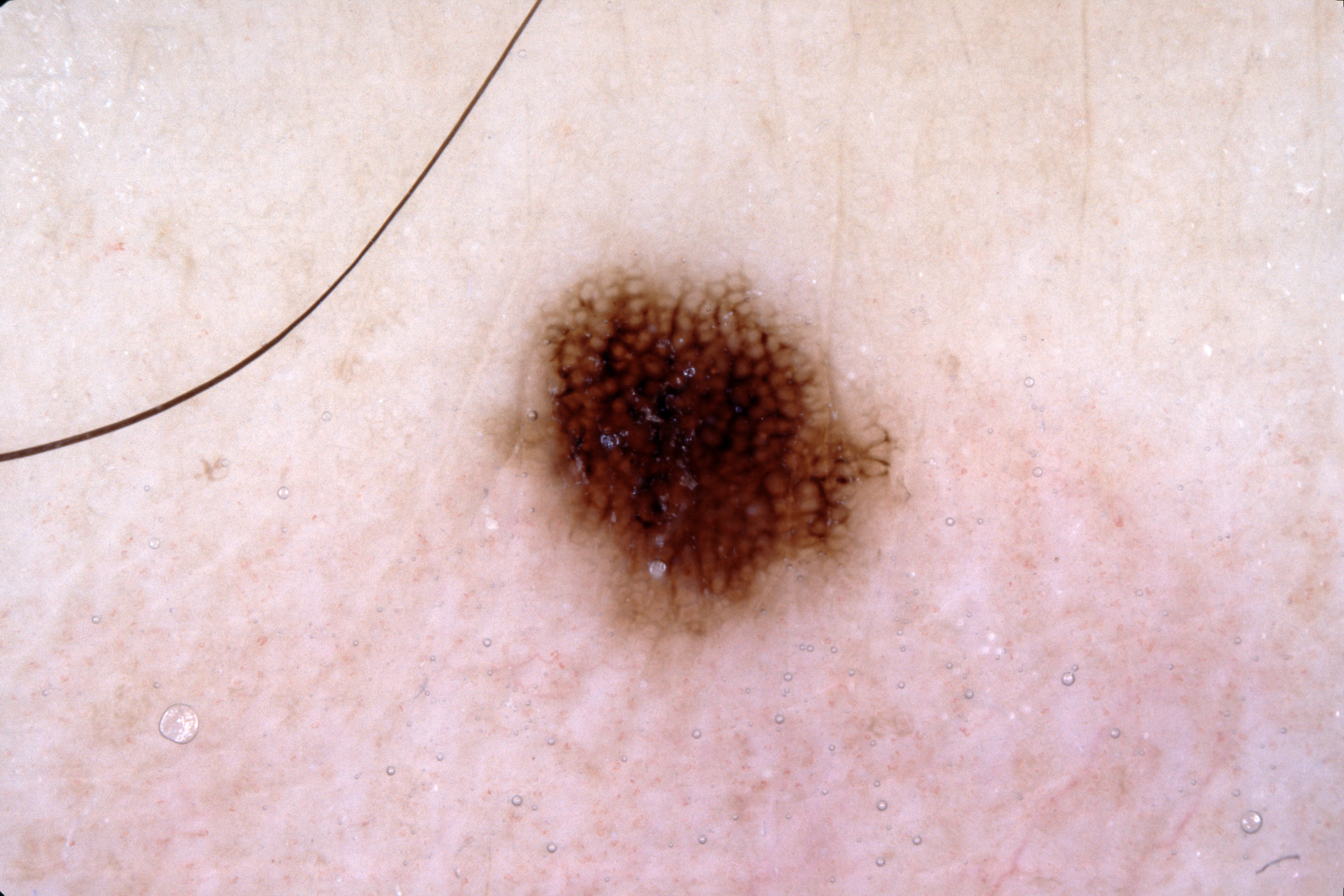A dermoscopic image of a skin lesion. Dermoscopic review identifies pigment network; no streaks, milia-like cysts, or negative network. The lesion spans box(494, 266, 903, 651). The lesion occupies roughly 9% of the field. Expert review diagnosed this as a melanocytic nevus, a benign skin lesion.